This is a close-up image. Female patient, age 18–29.
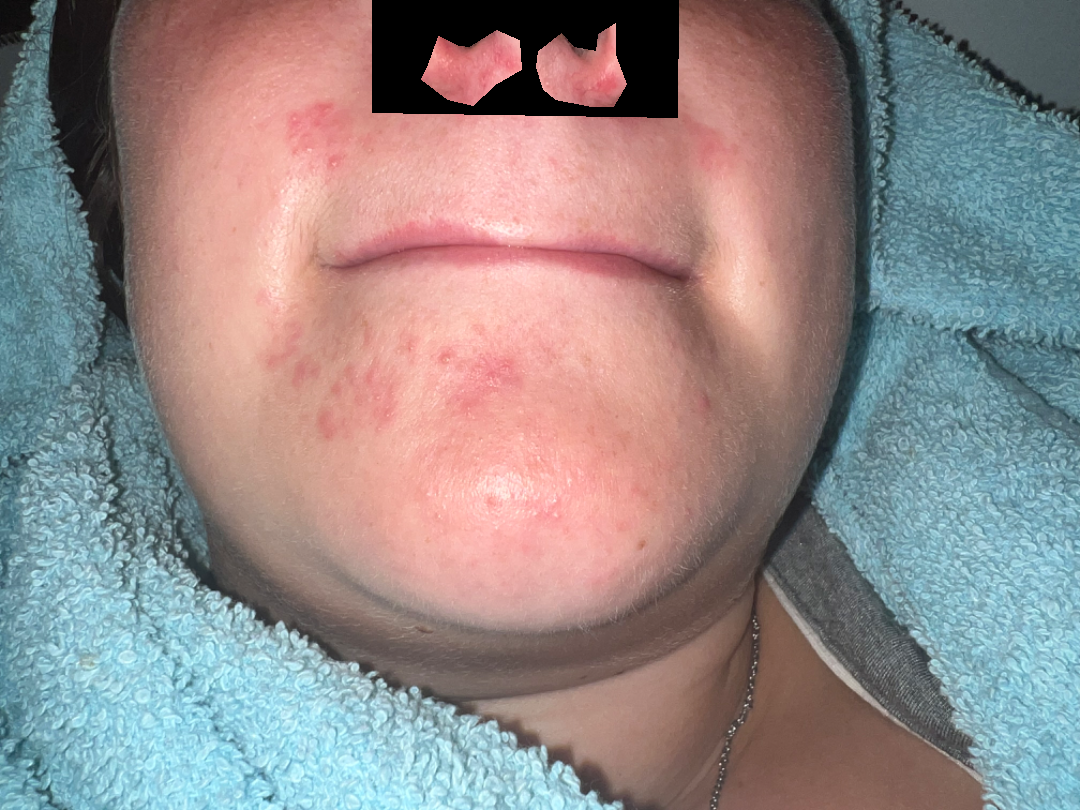Findings:
- assessment · the impression is Perioral Dermatitis